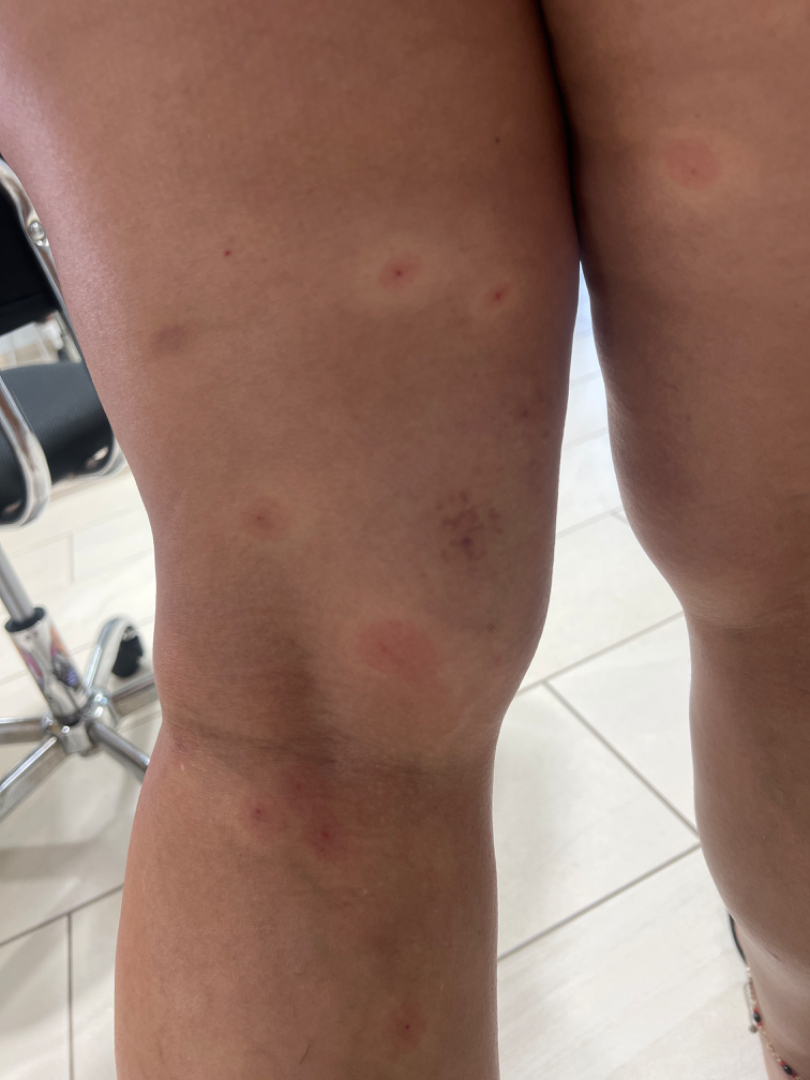History:
No constitutional symptoms were reported. The lesion involves the leg. Present for about one day. The subject is 40–49, female. The photograph is a close-up of the affected area. The lesion is described as flat. The patient described the issue as skin that appeared healthy to them. The patient did not report lesion symptoms.
Impression:
On photographic review, the leading impression is Insect Bite; also raised was Erythema multiforme.